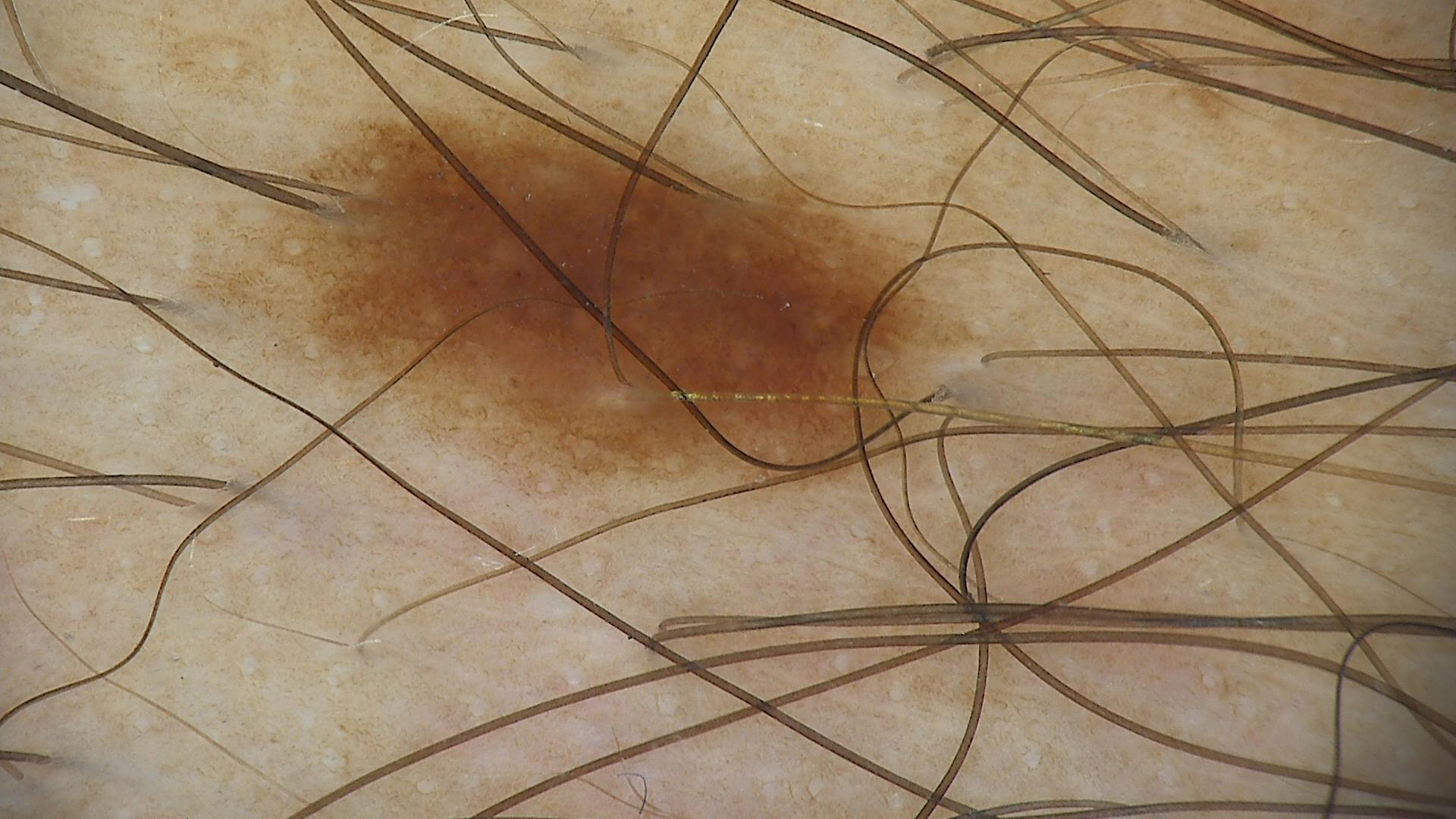Q: What kind of image is this?
A: dermoscopy
Q: What was the diagnostic impression?
A: dysplastic junctional nevus (expert consensus)